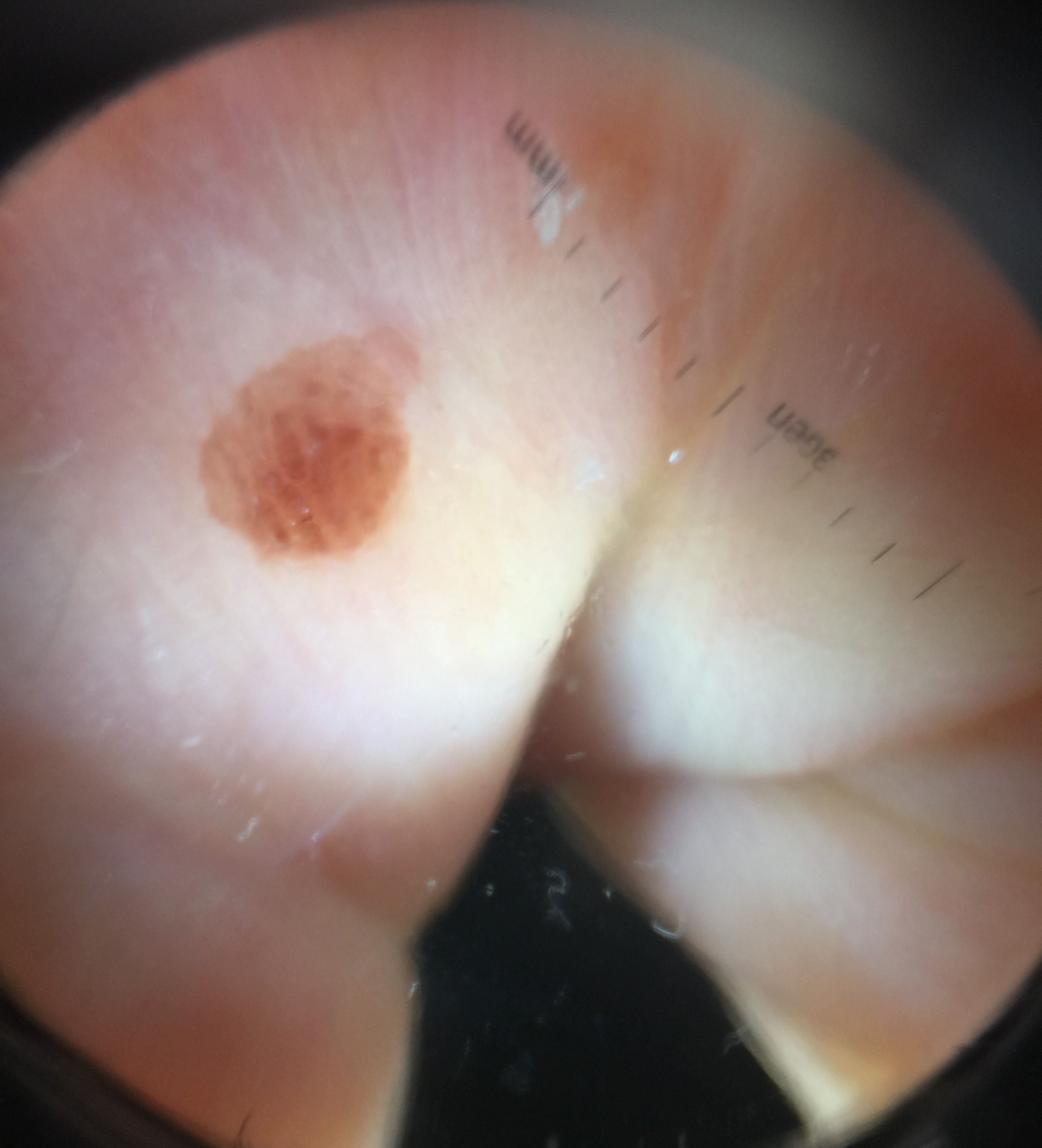Labeled as an acral junctional nevus.